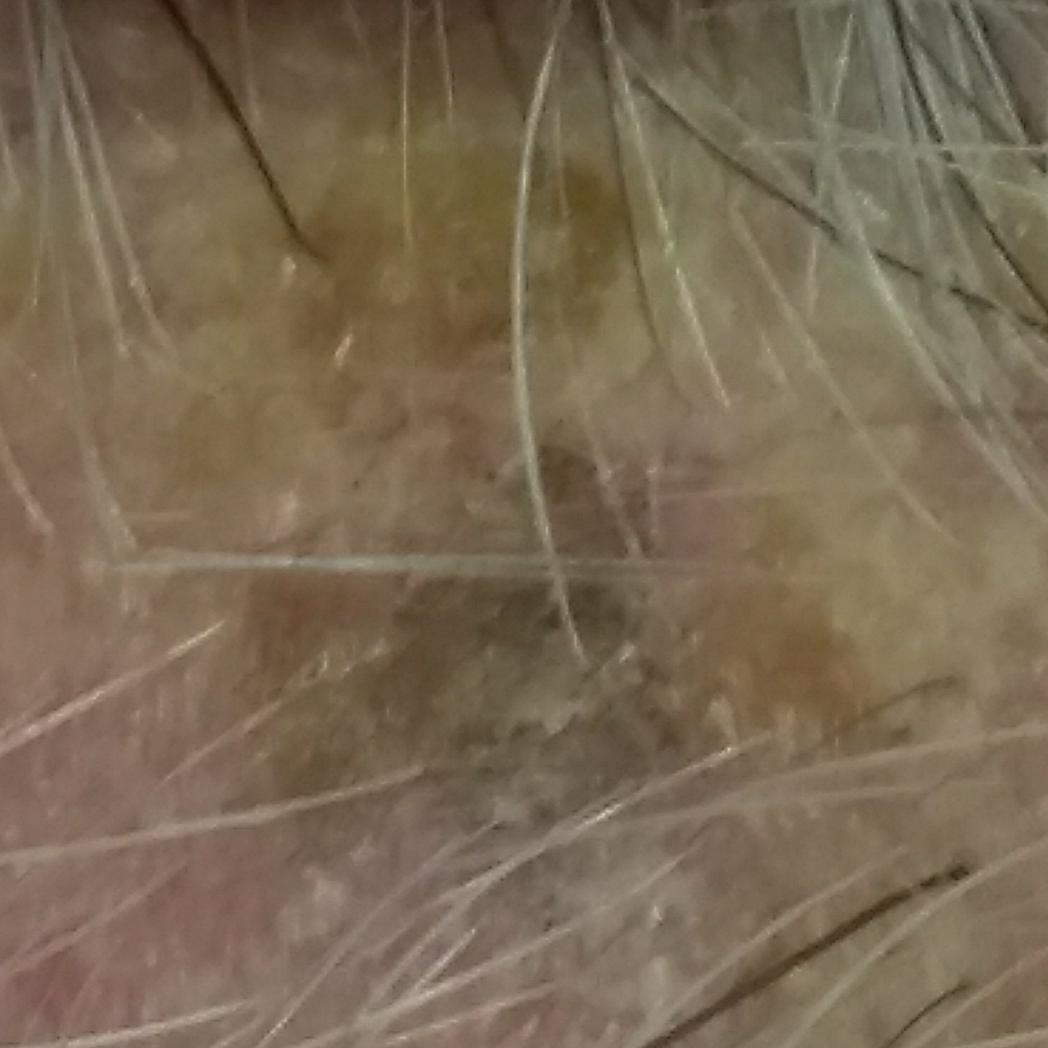impression = seborrheic keratosis (clinical consensus).